A dermoscopic image of a skin lesion.
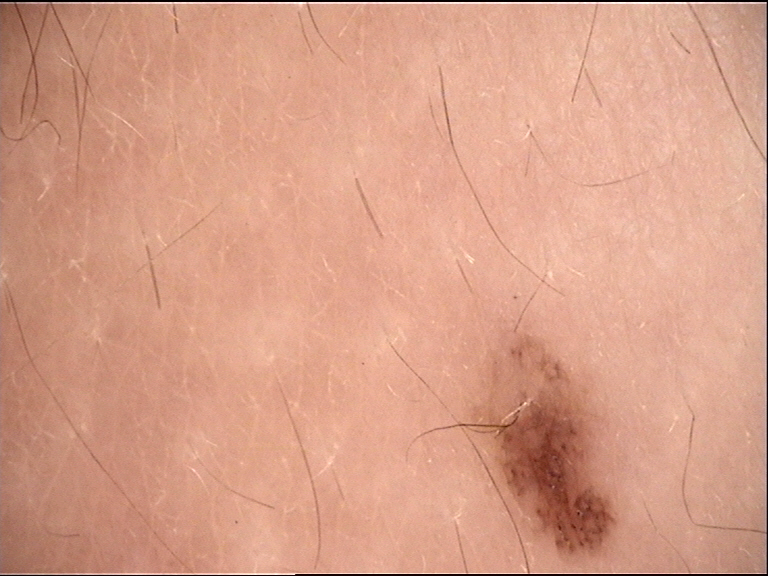diagnosis = dysplastic junctional nevus (expert consensus)